A dermoscopic photograph of a skin lesion:
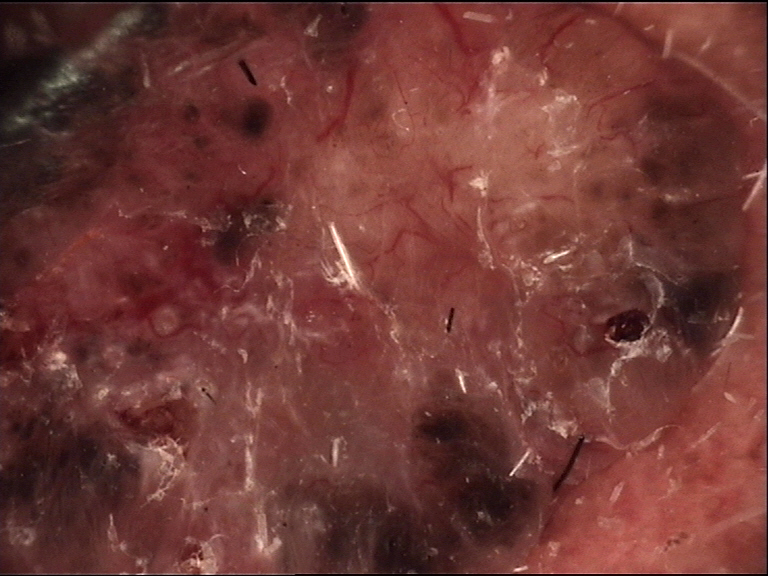– subtype · keratinocytic
– pathology · basal cell carcinoma (biopsy-proven)